This image was taken at an angle · the patient is 40–49, male · skin tone: self-reported FST III; lay graders estimated Monk Skin Tone 3–4 · the affected area is the leg · no associated systemic symptoms reported · the lesion is associated with itching · the condition has been present for less than one week · the lesion is described as raised or bumpy · self-categorized by the patient as a rash — 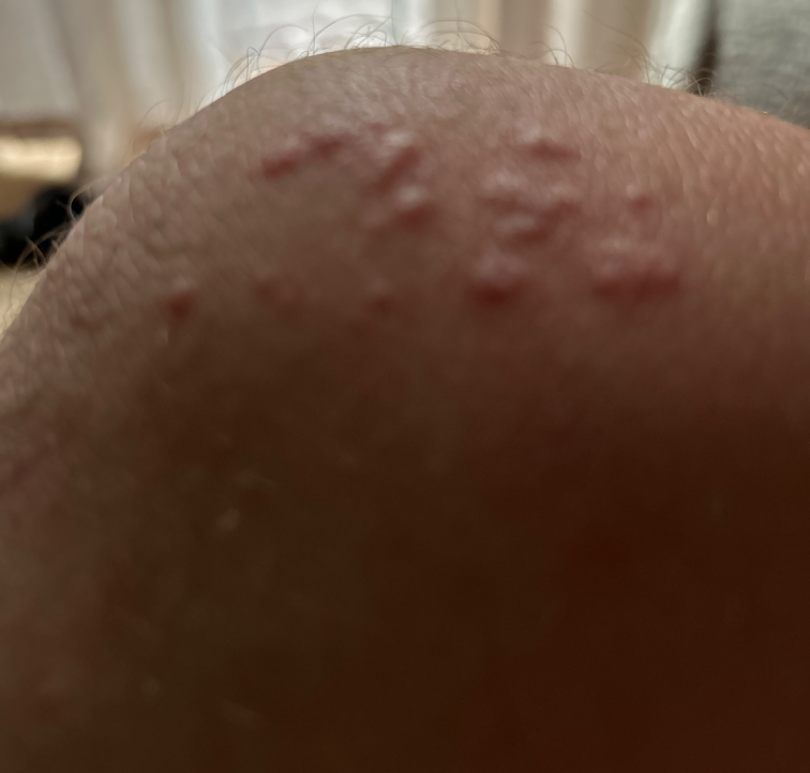  assessment: ungradable on photographic review